A dermatoscopic image of a skin lesion; a female patient age 27: 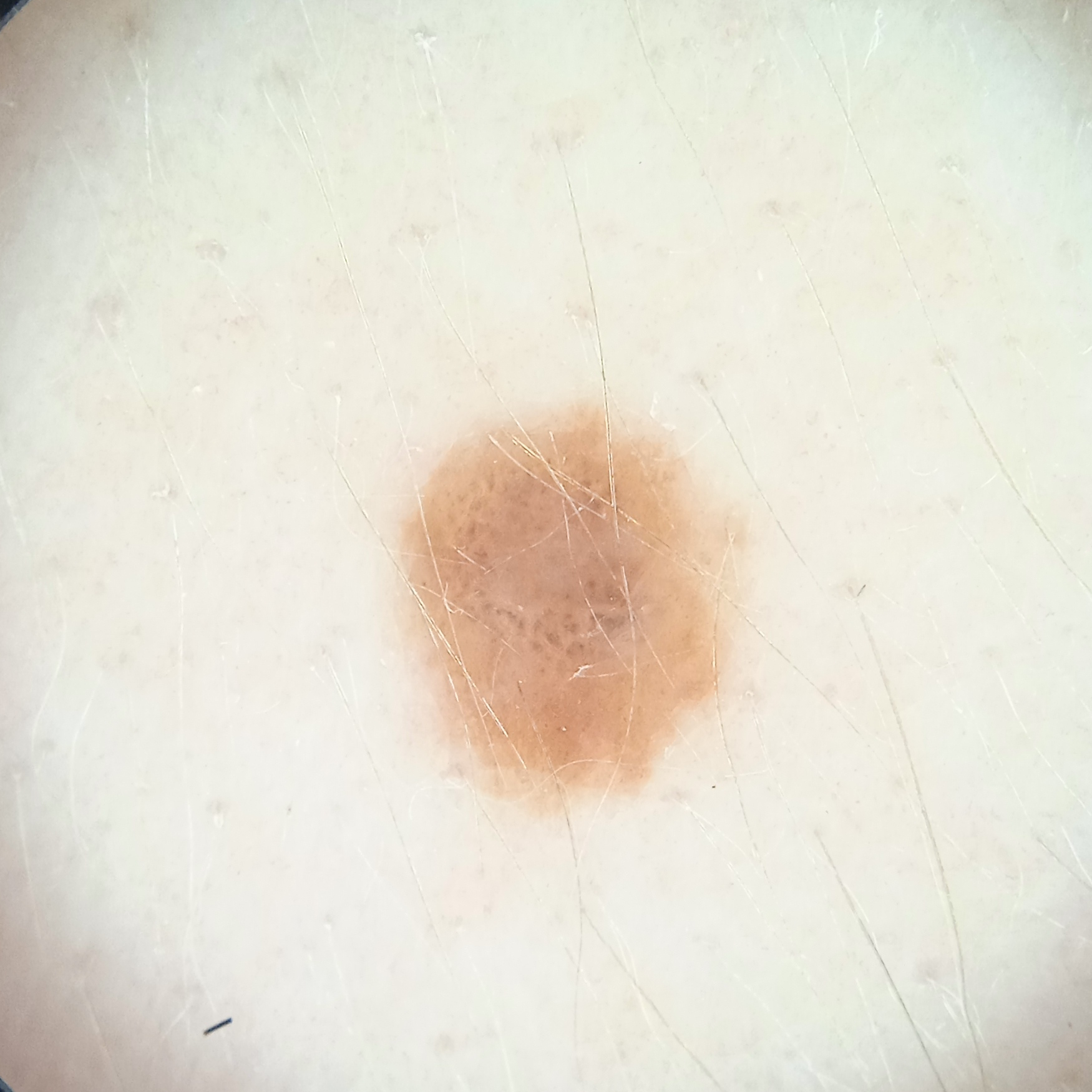Case:
* body site · the torso
* lesion size · 4.4 mm
* assessment · melanocytic nevus (dermatologist consensus)